A dermoscopic close-up of a skin lesion:
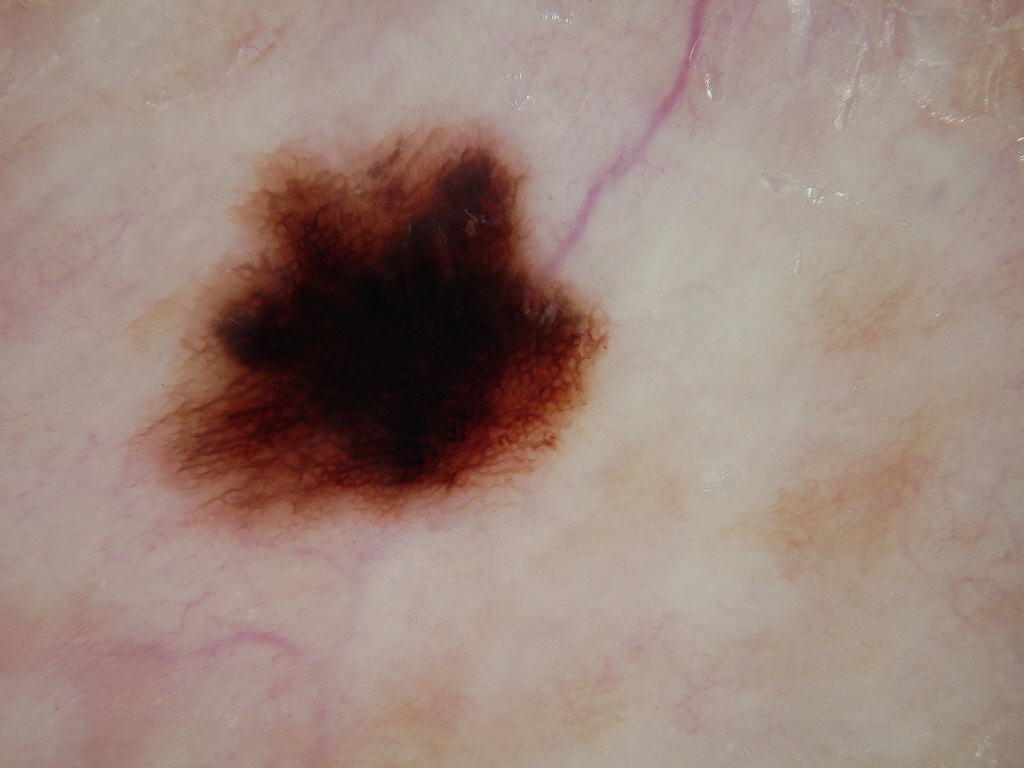lesion bbox — <box>121, 102, 631, 565</box> | assessment — a melanocytic nevus.